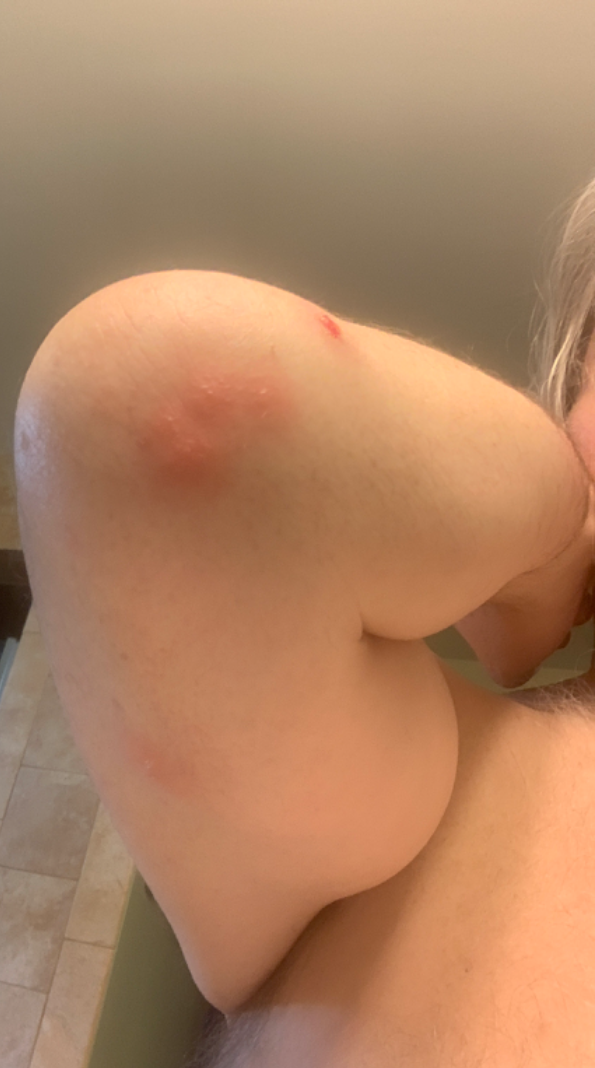Review:
The reviewer was unable to grade this case for skin condition.
Patient information:
The patient indicates the lesion is raised or bumpy. This image was taken at a distance. The arm is involved. Skin tone: FST II. Reported duration is less than one week. The patient is 60–69, male. Symptoms reported: itching.